Symptoms reported: enlargement and itching. Located on the back of the torso. No relevant systemic symptoms. The lesion is described as raised or bumpy. A close-up photograph. The patient is 18–29, male. The patient described the issue as a rash: 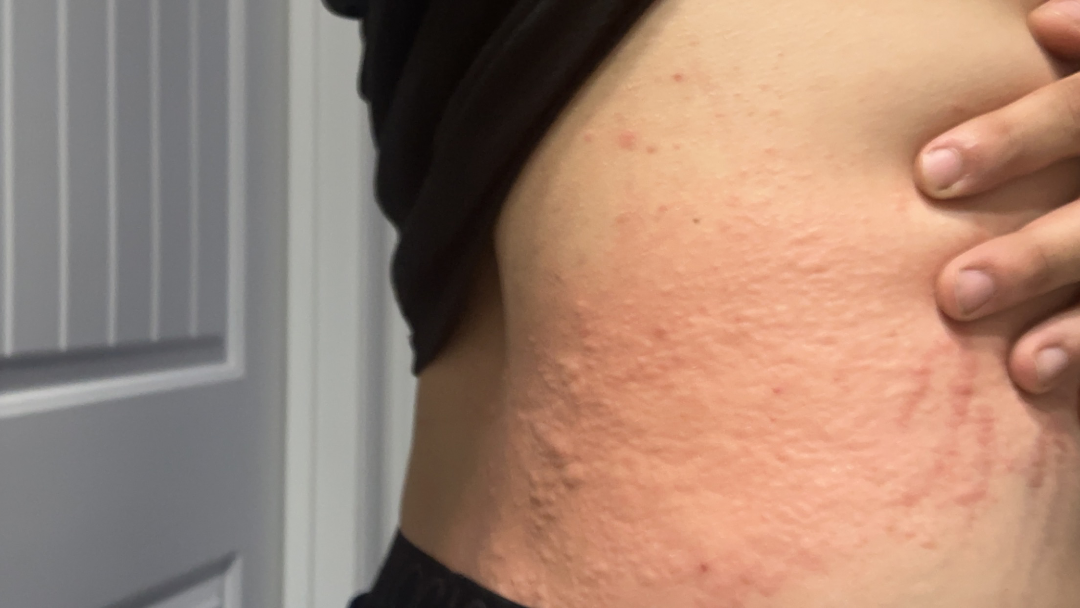impression: most consistent with Urticaria